A dermoscopic close-up of a skin lesion.
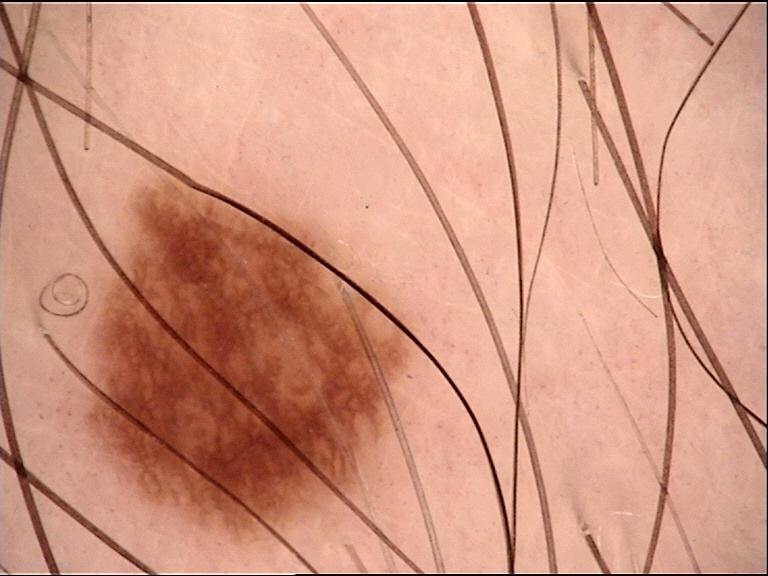The diagnosis was a benign lesion — a dysplastic junctional nevus.